The arm is involved, this is a close-up image:
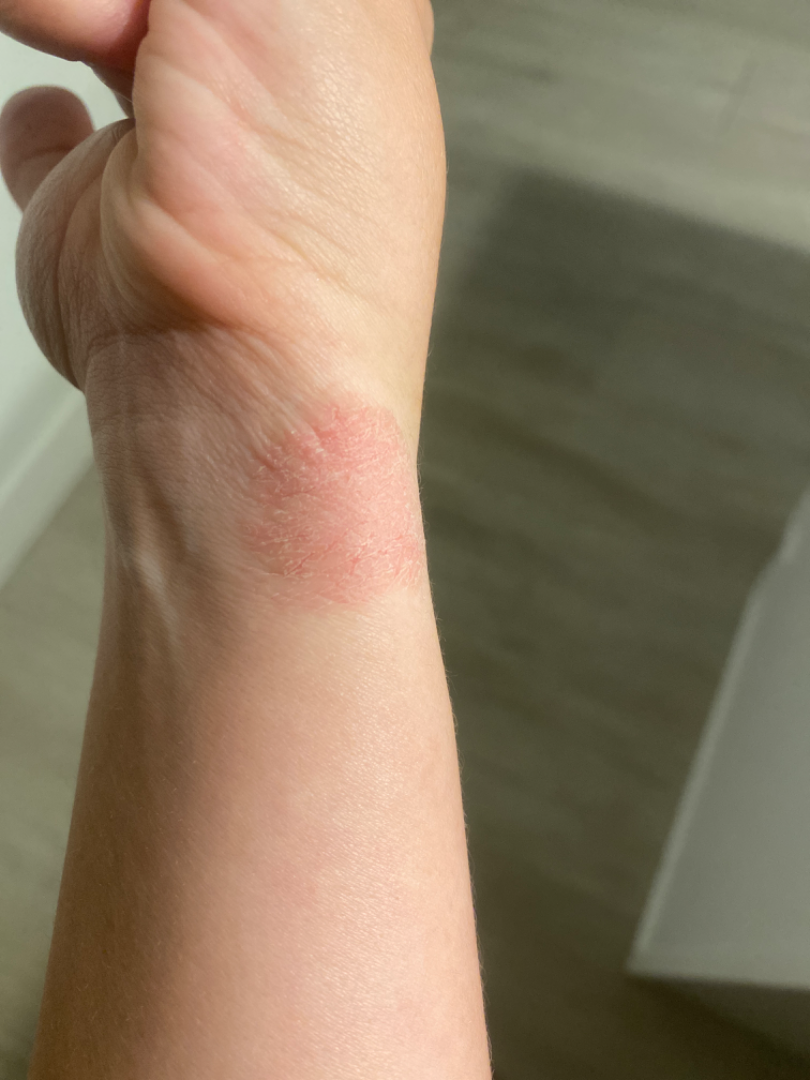Q: Duration?
A: about one day
Q: Patient's own categorization?
A: a rash
Q: Constitutional symptoms?
A: none reported
Q: What is the lesion texture?
A: rough or flaky
Q: What conditions are considered?
A: most likely Eczema; also raised was Psoriasis; less probable is Tinea